The patient is 50–59, male · the photograph was taken at an angle.
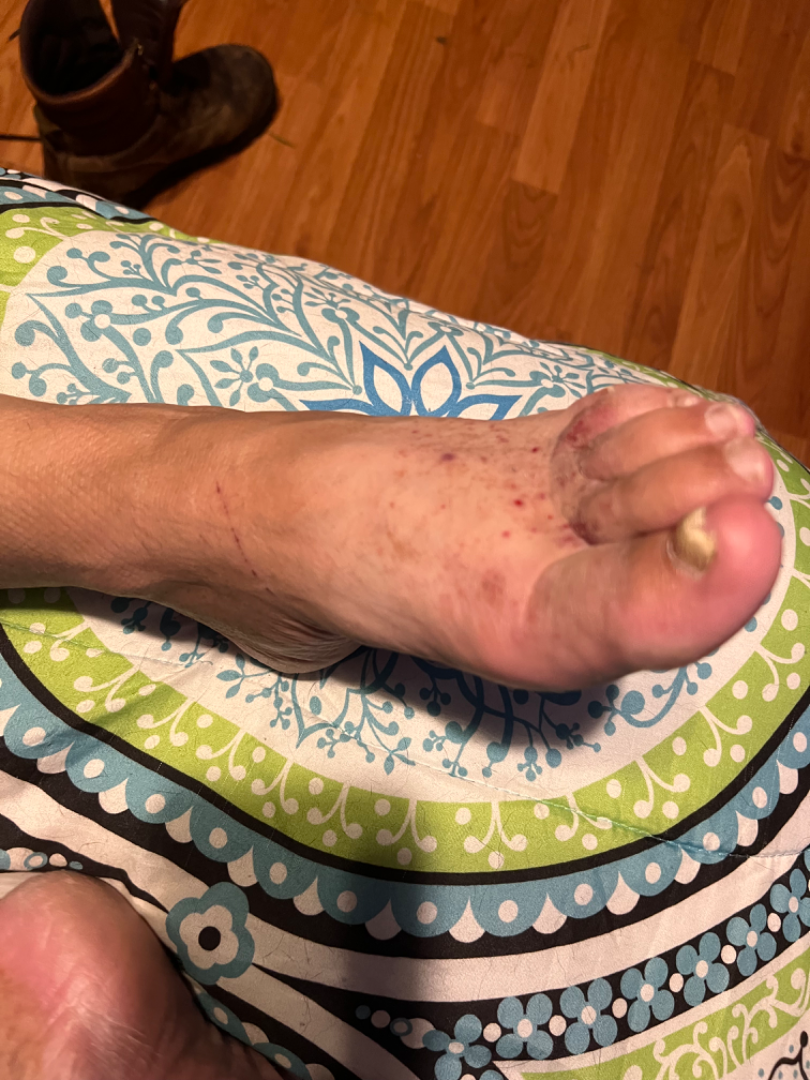assessment: not assessable | skin tone: self-reported Fitzpatrick phototype III; lay graders estimated MST 5 (US pool) or 3 (India pool) | reported symptoms: itching, bleeding and burning | associated systemic symptoms: none reported | onset: one to four weeks | lesion texture: rough or flaky.